A dermatoscopic image of a skin lesion:
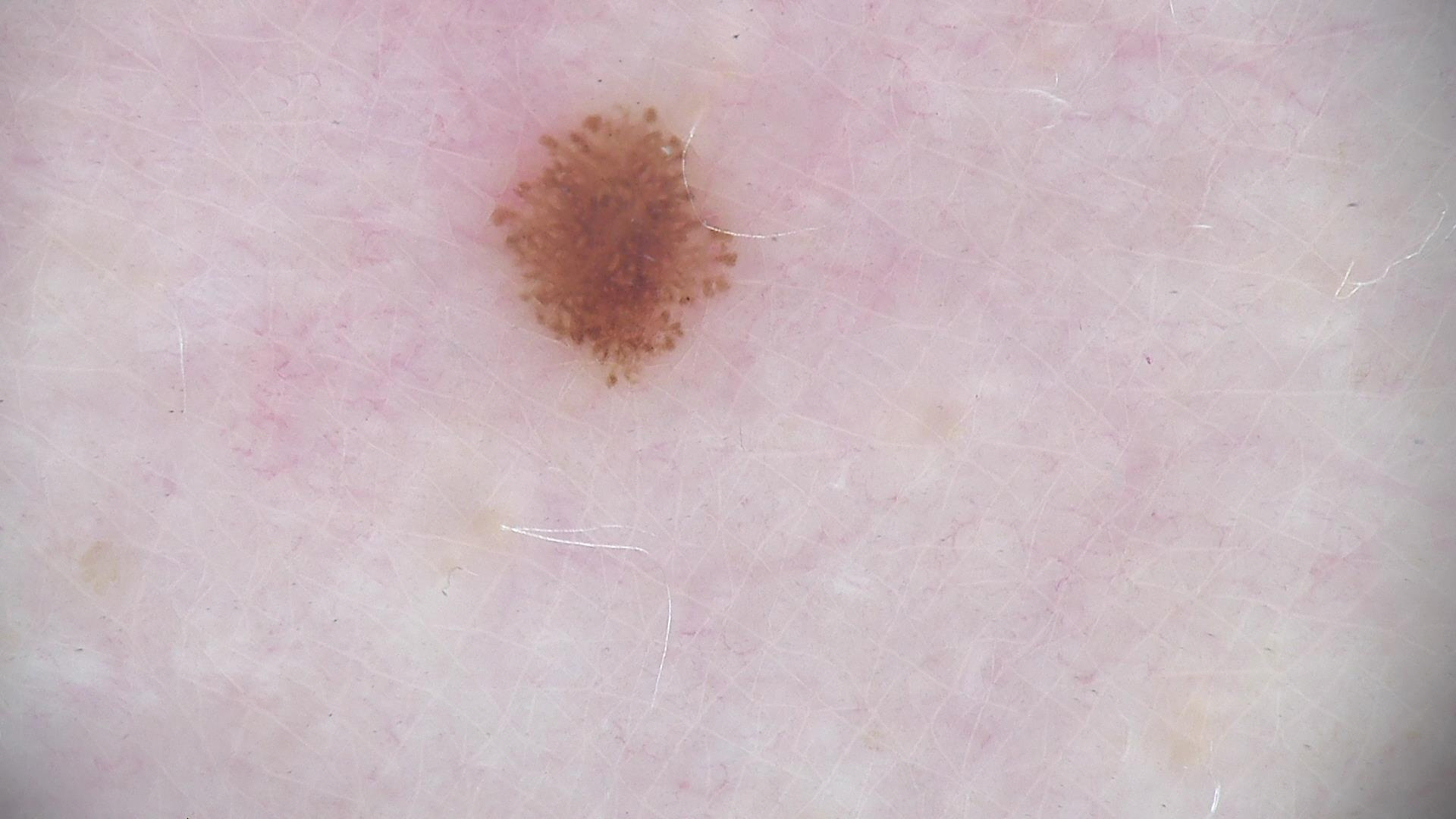Impression: The diagnostic label was a benign lesion — a dysplastic junctional nevus.